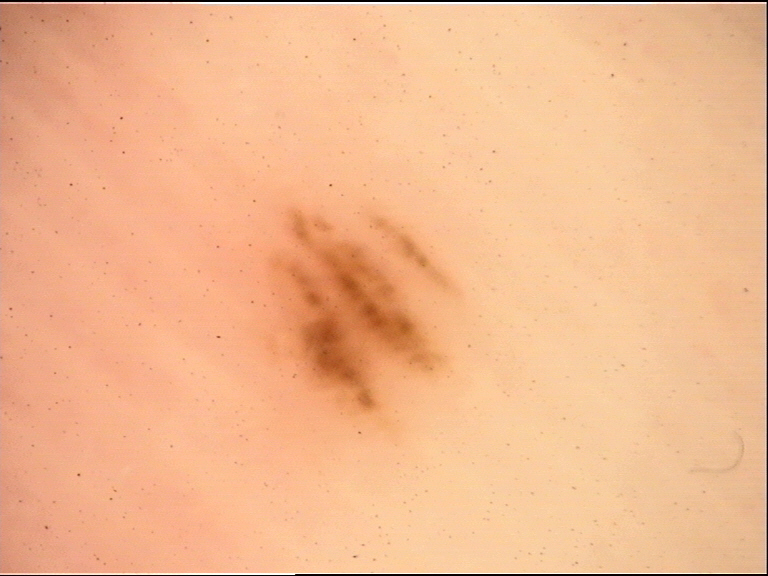Classified as an acral junctional nevus.